Female patient, age 60–69; located on the front of the torso and back of the torso; close-up view; the lesion is described as raised or bumpy; the condition has been present for less than one week; symptoms reported: bothersome appearance; the patient described the issue as a rash; no constitutional symptoms were reported:
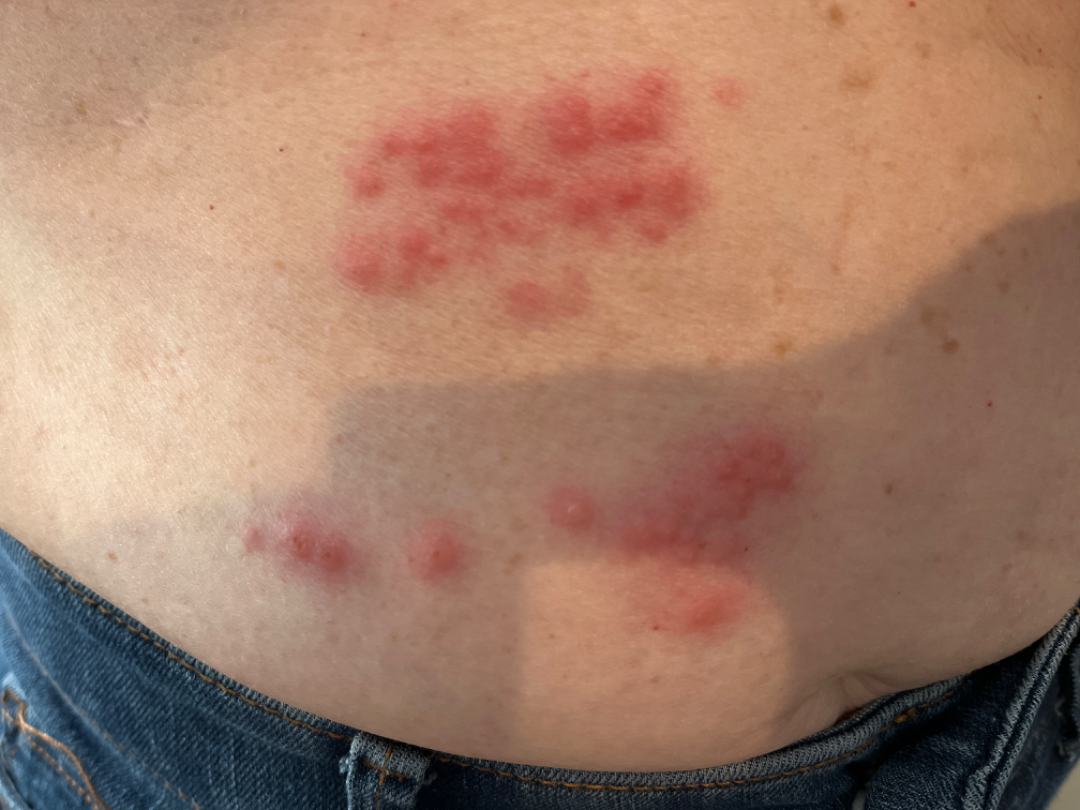On teledermatology review: most likely Herpes Zoster.